A dermoscopic close-up of a skin lesion: 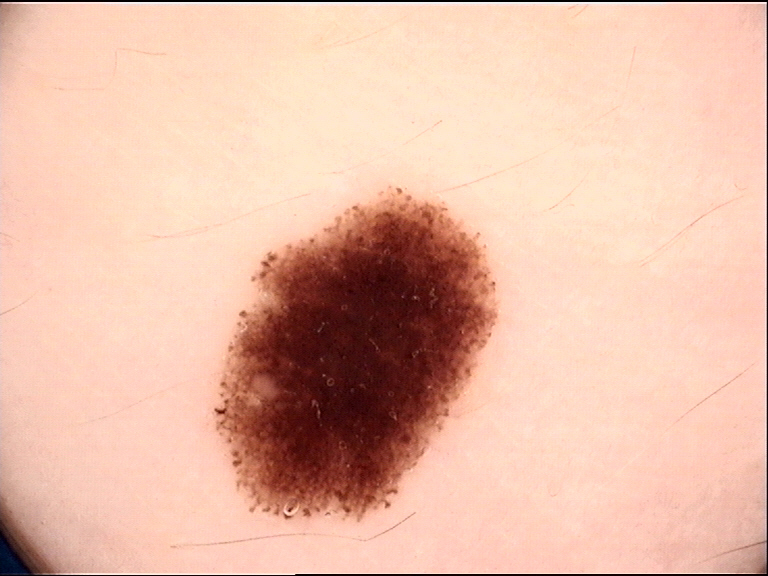label=dysplastic junctional nevus (expert consensus).